A dermoscopic photograph of a skin lesion.
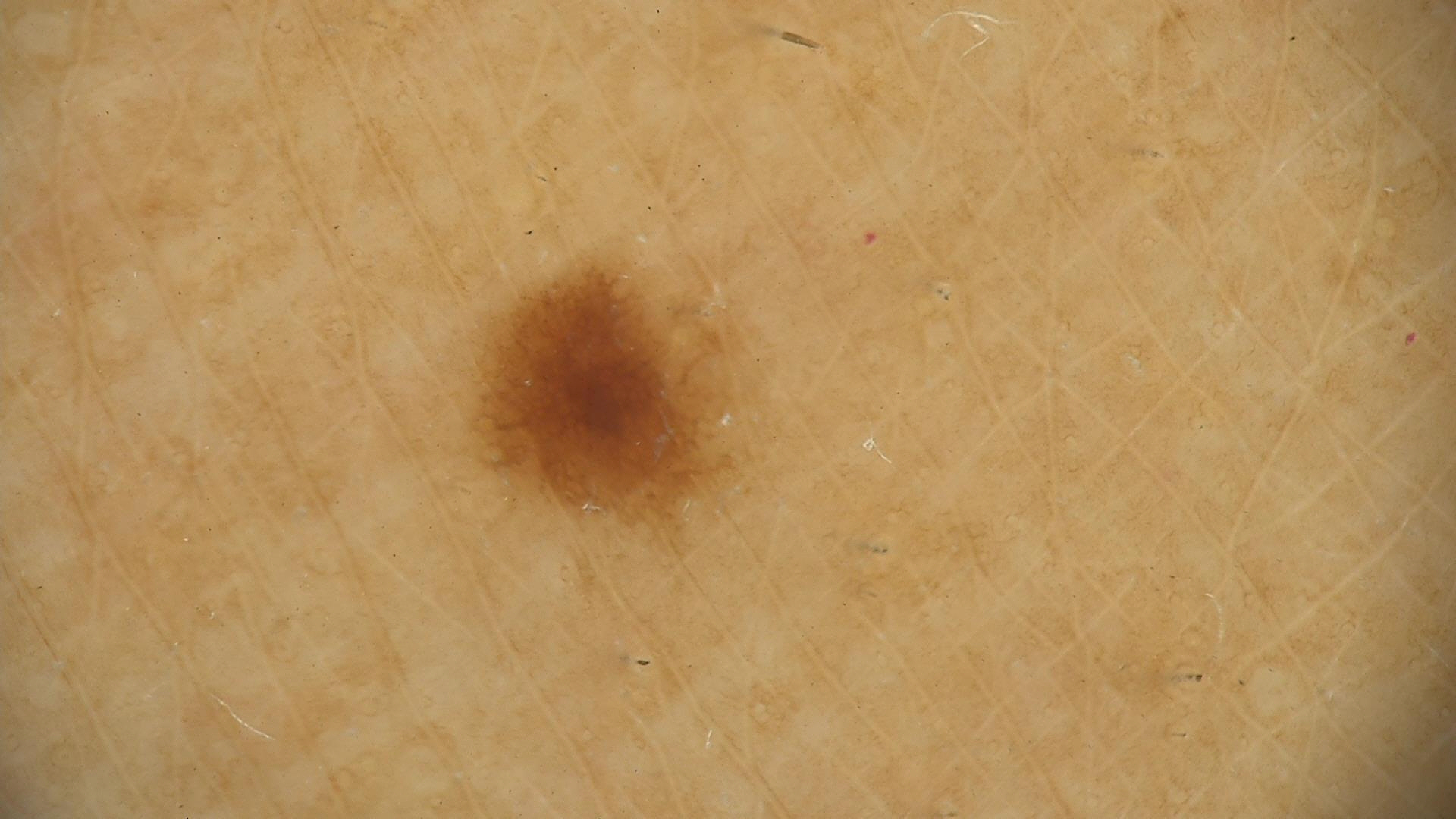assessment — dysplastic junctional nevus (expert consensus).